This image was taken at an angle · the subject is 18–29, female: 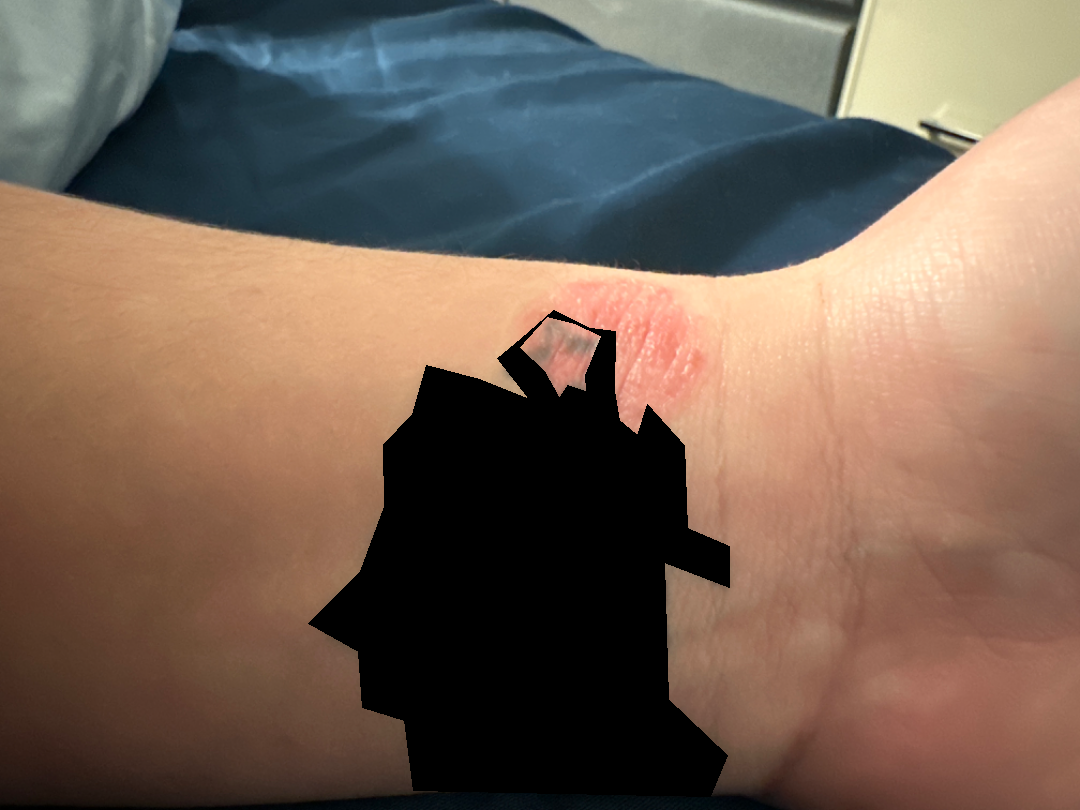• impression — the differential includes Eczema, Psoriasis and Allergic Contact Dermatitis, with no clear leading consideration